The photo was captured at an angle — 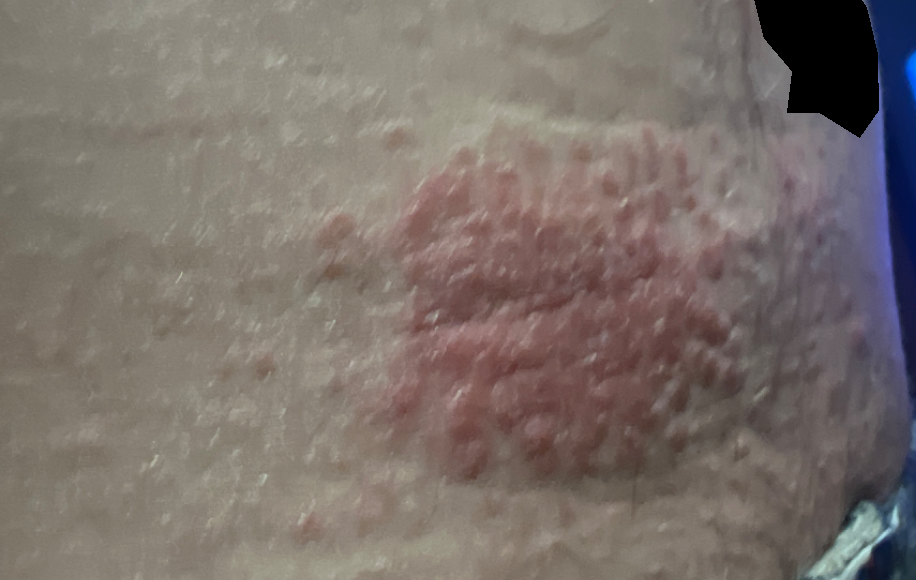Diagnostic features were not clearly distinguishable in this photograph.